A skin lesion imaged with a dermatoscope.
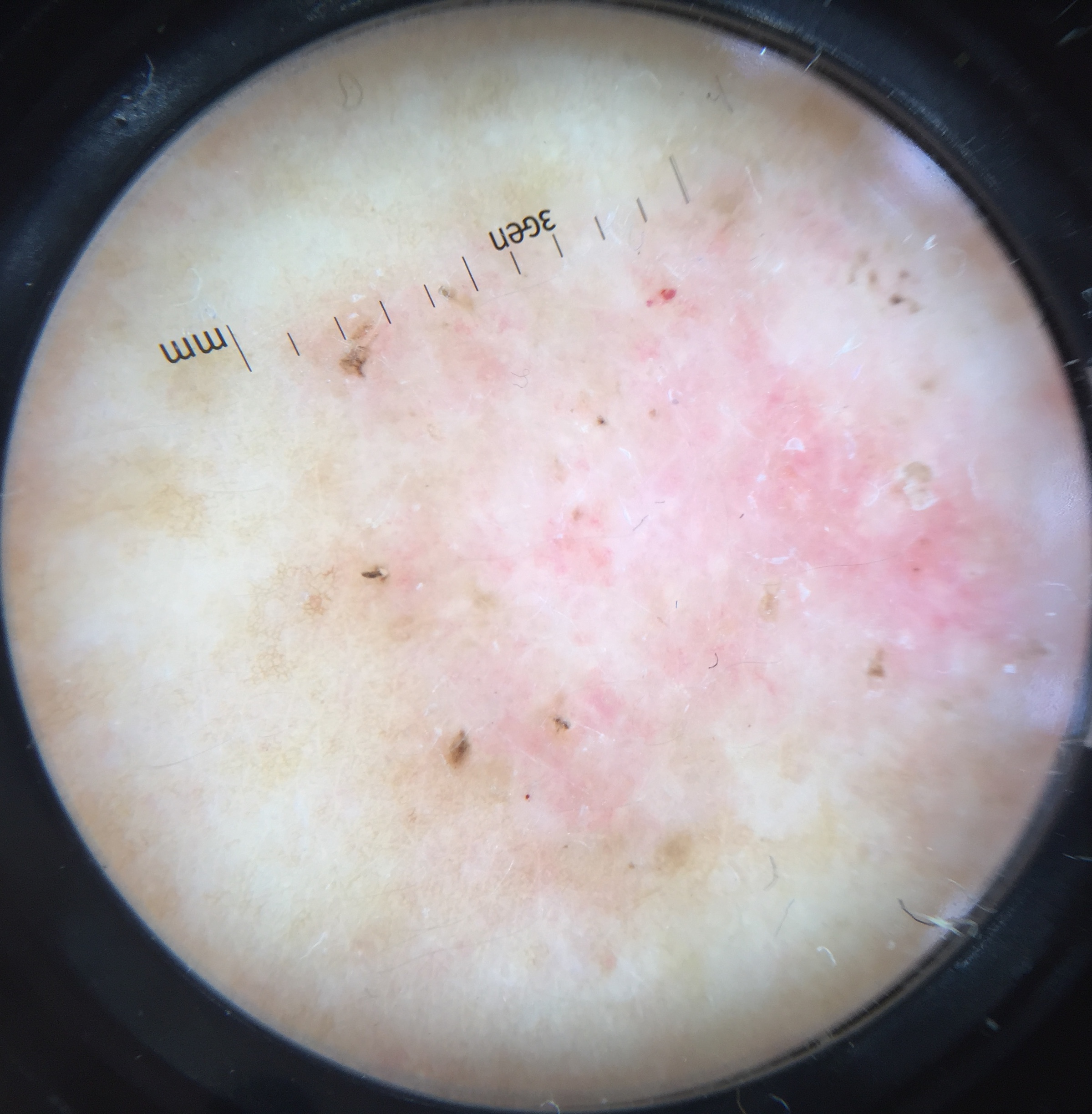subtype: keratinocytic | pathology: basal cell carcinoma (biopsy-proven).